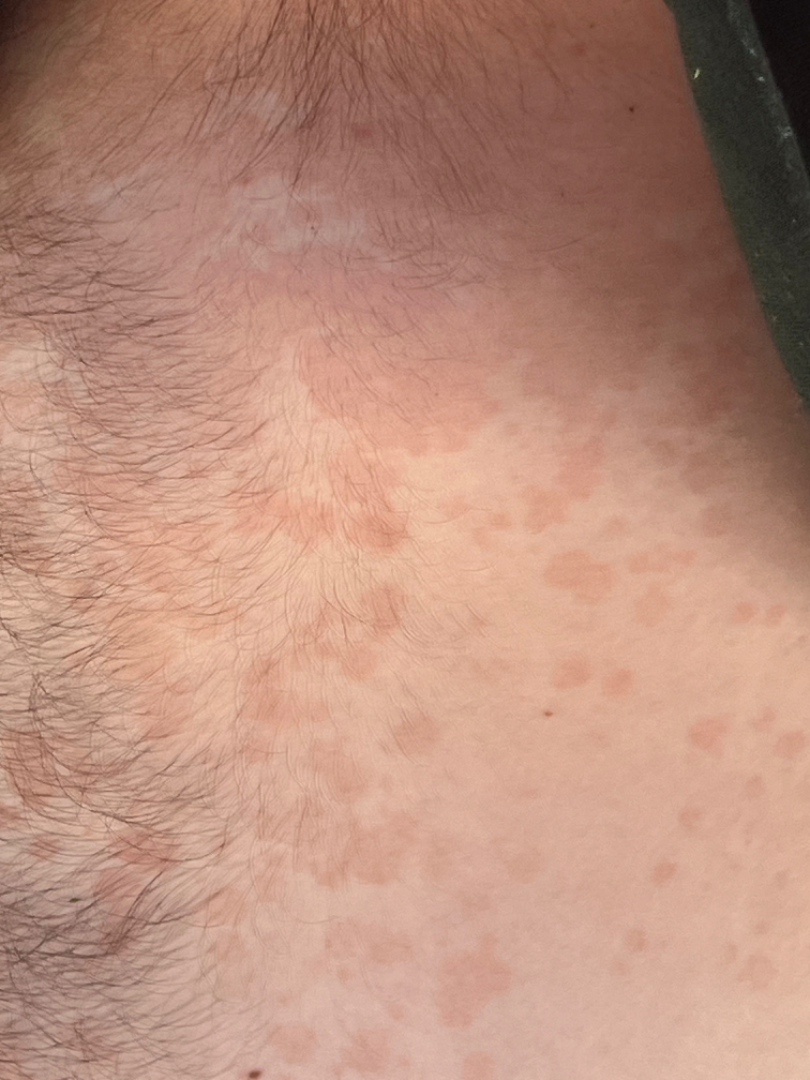This is a close-up image. The patient indicates the lesion is flat. The lesion involves the back of the torso and front of the torso. No constitutional symptoms were reported. Reported duration is one to three months. Self-categorized by the patient as a rash. The subject is a male aged 18–29. The patient reported no relevant symptoms from the lesion. The reviewing clinician's impression was: consistent with Tinea Versicolor.